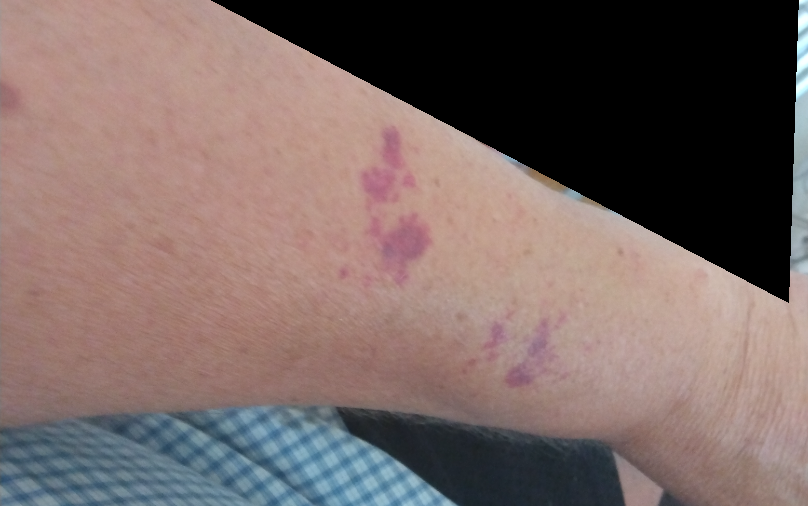No differential diagnosis could be assigned on photographic review. The photo was captured at a distance. No relevant systemic symptoms. Fitzpatrick III; lay graders estimated 2 on the Monk skin tone scale. Located on the arm. Symptoms reported: enlargement. The patient reports the lesion is flat.